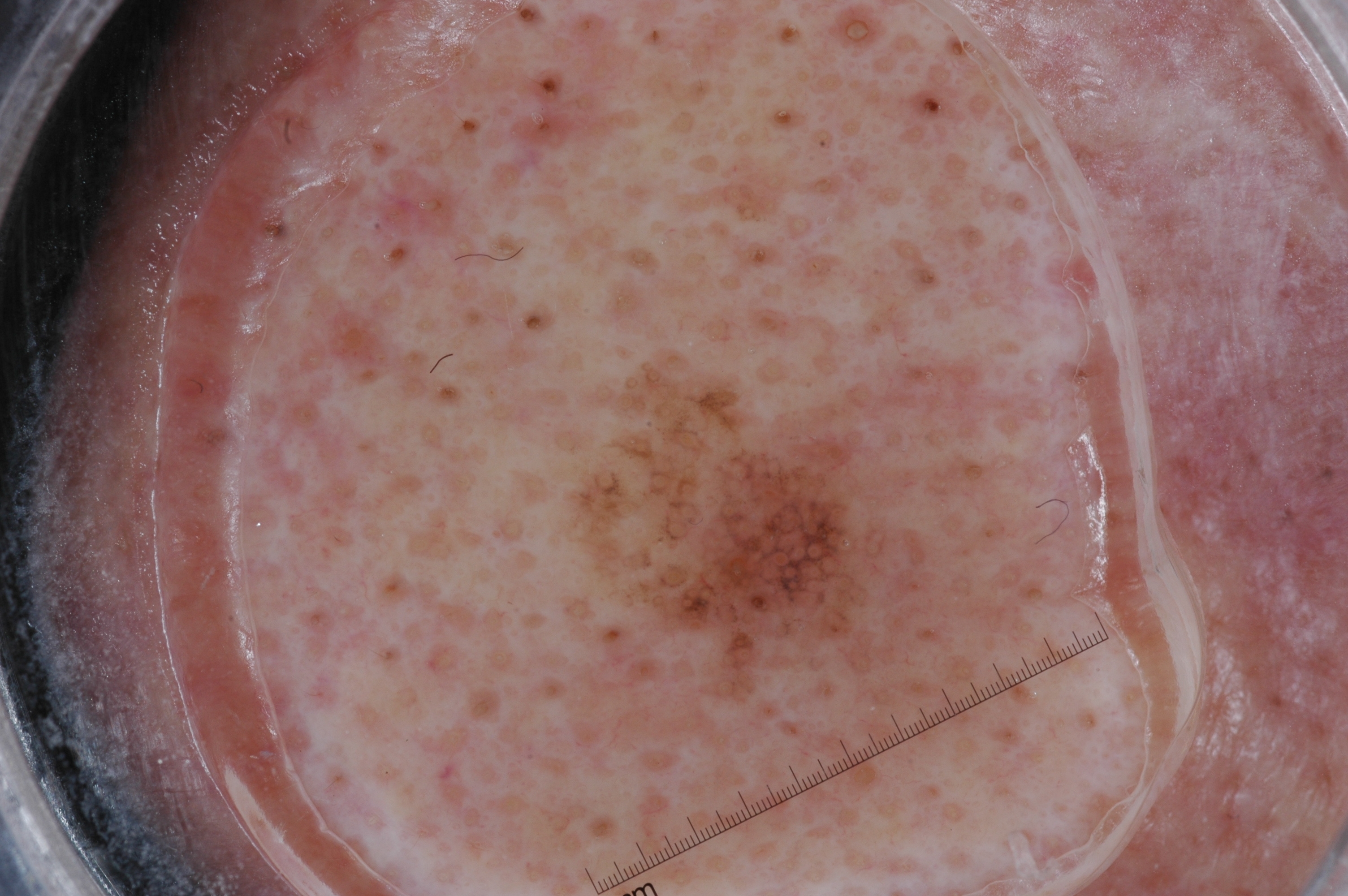A dermoscopic view of a skin lesion.
In (x1, y1, x2, y2) order, the lesion spans box(564, 347, 905, 703).
Confirmed on histopathology as a melanoma.